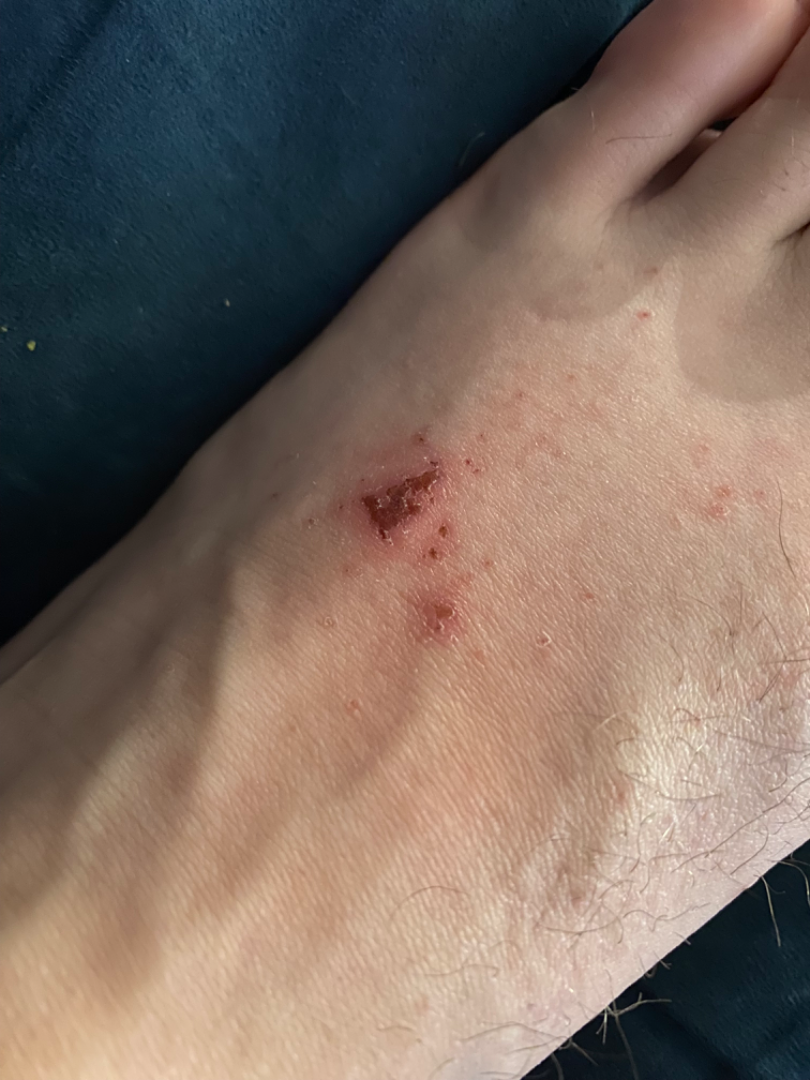On photographic review by a dermatologist: Allergic Contact Dermatitis (possible); Irritant Contact Dermatitis (possible).